The leg is involved · a close-up photograph · the contributor is a male aged 40–49: 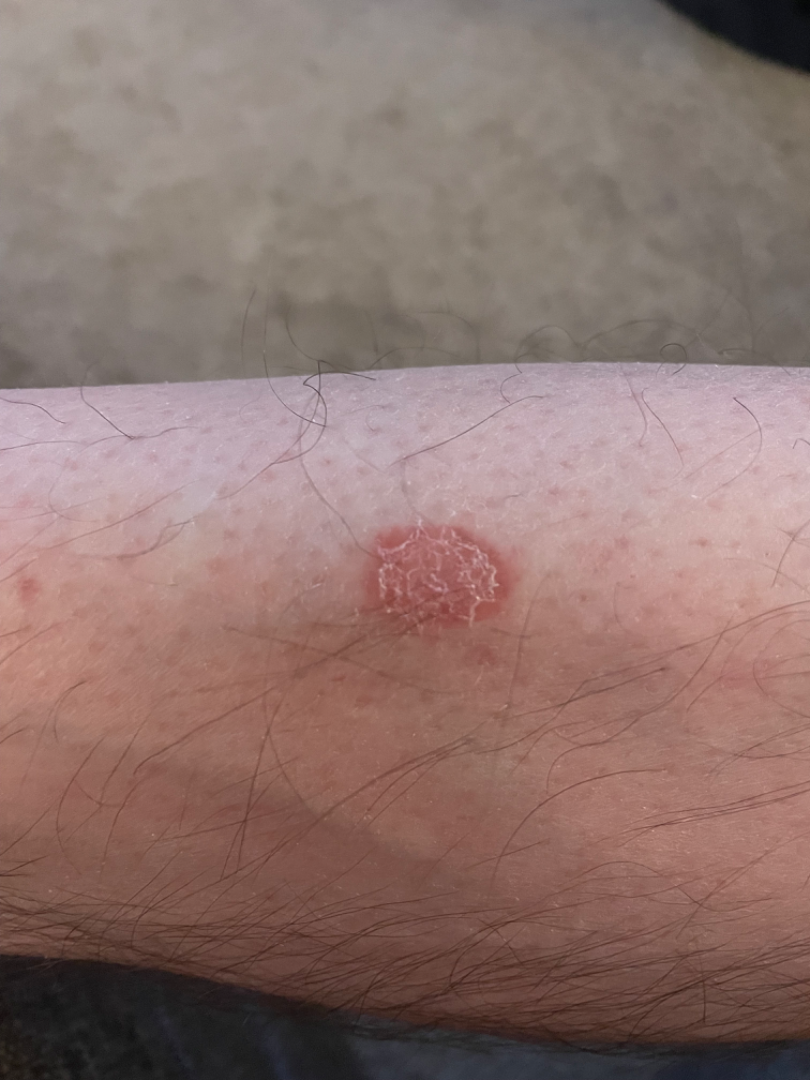assessment = could not be assessed